An image taken at an angle; located on the arm: 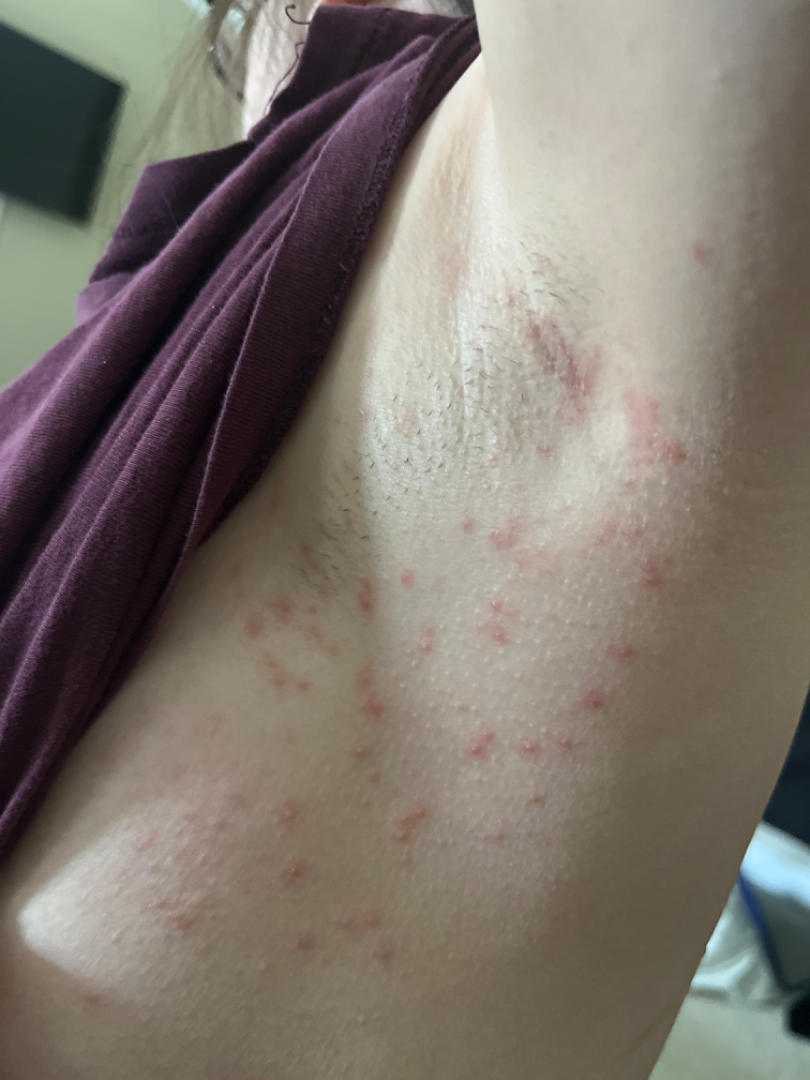assessment = unable to determine.